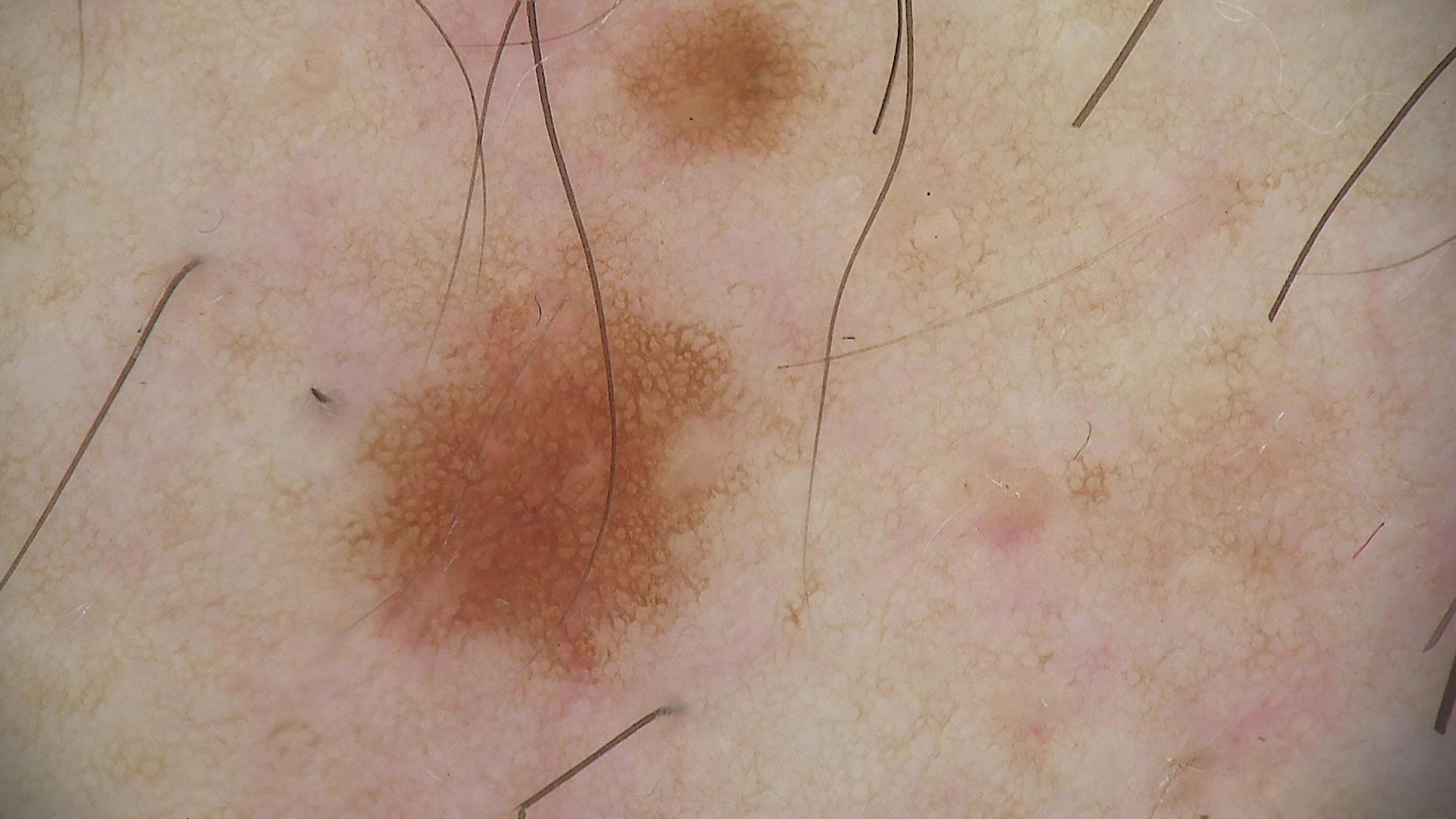A dermoscopy image of a single skin lesion. The architecture is that of a banal lesion. Classified as a junctional nevus.